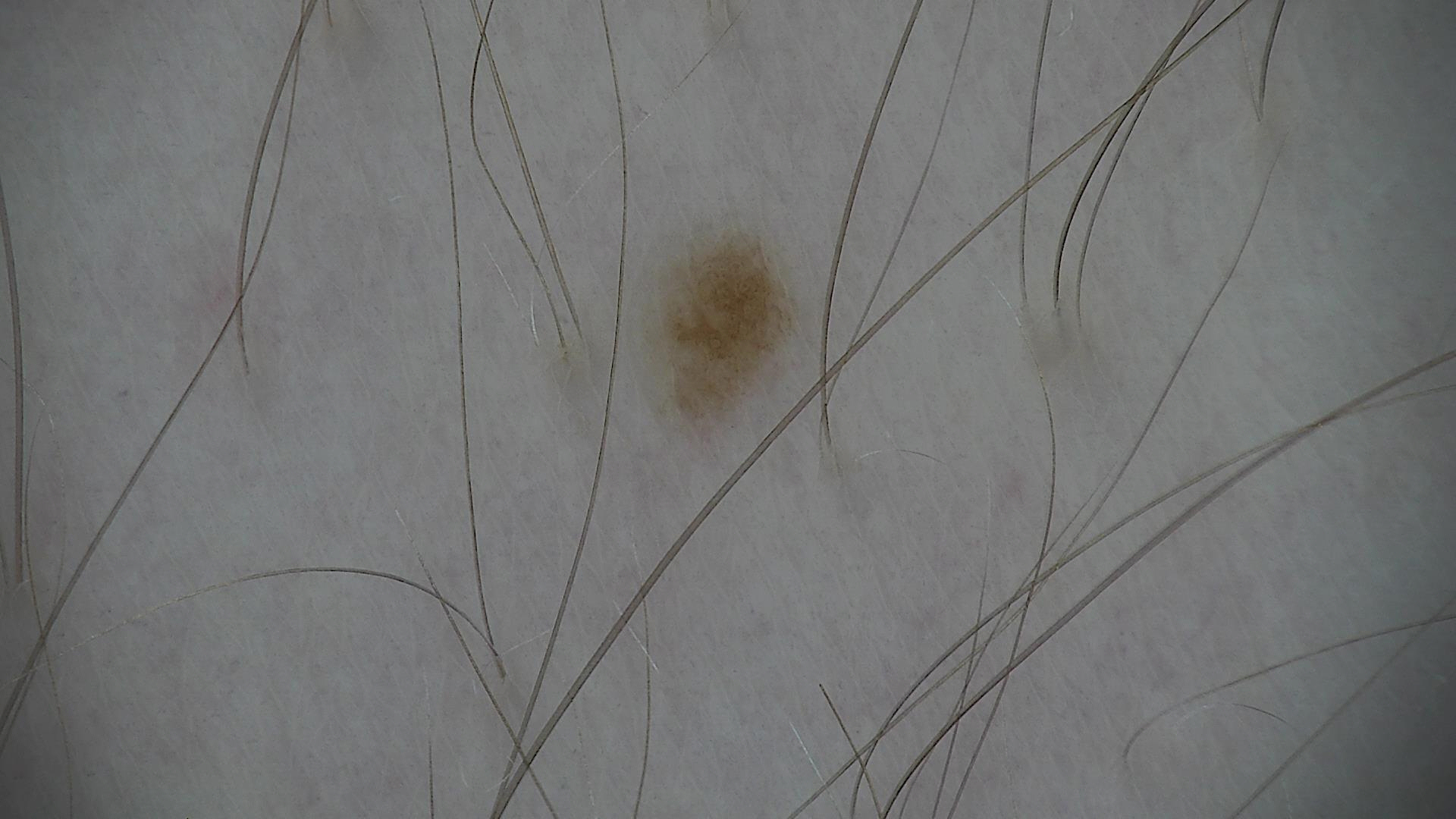  diagnosis:
    name: dysplastic junctional nevus
    code: jd
    malignancy: benign
    super_class: melanocytic
    confirmation: expert consensus